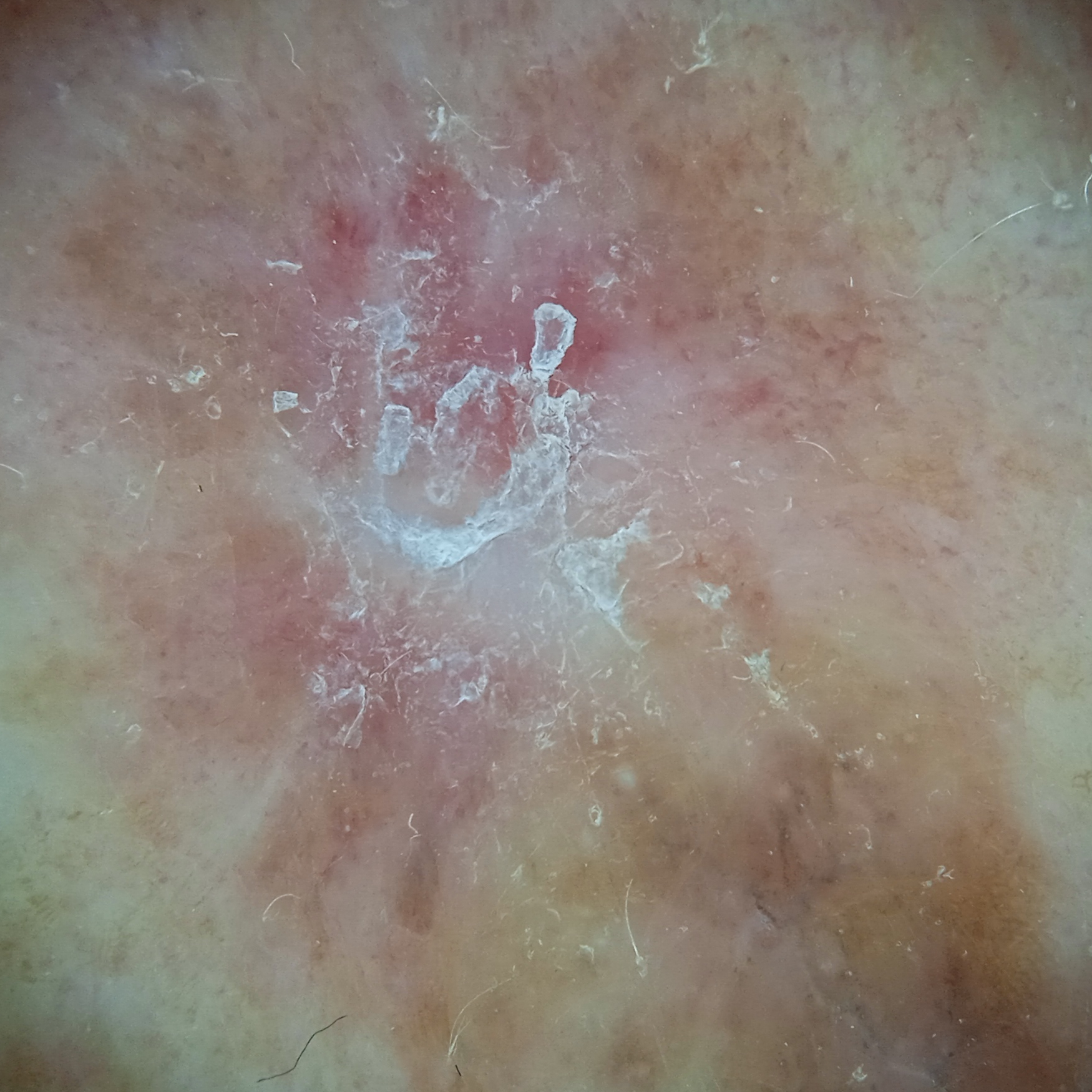| feature | finding |
|---|---|
| image type | dermoscopy |
| clinical context | research study (no referral diagnosis) |
| patient | male, aged 62 |
| sun reaction | skin reddens with sun exposure |
| nevus count | few melanocytic nevi overall |
| location | the back |
| diameter | 13.8 mm |
| diagnostic label | squamous cell carcinoma (dermatologist consensus) |